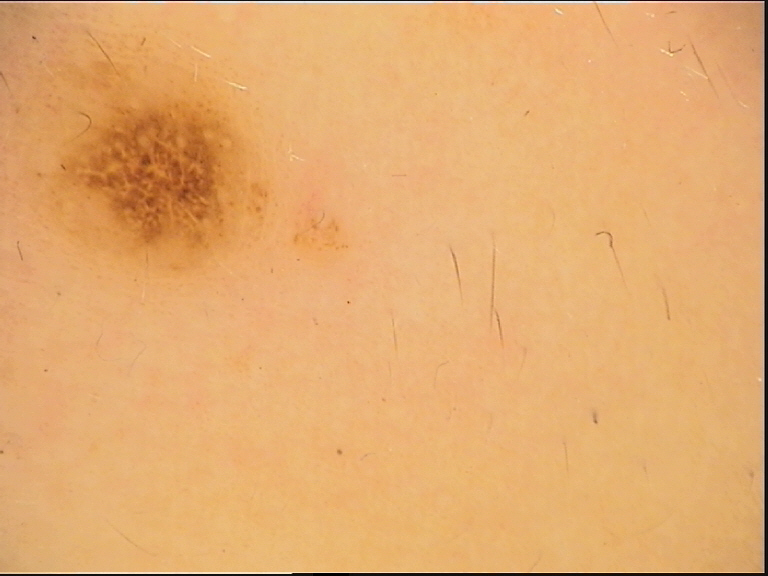Case:
- assessment — dysplastic compound nevus (expert consensus)